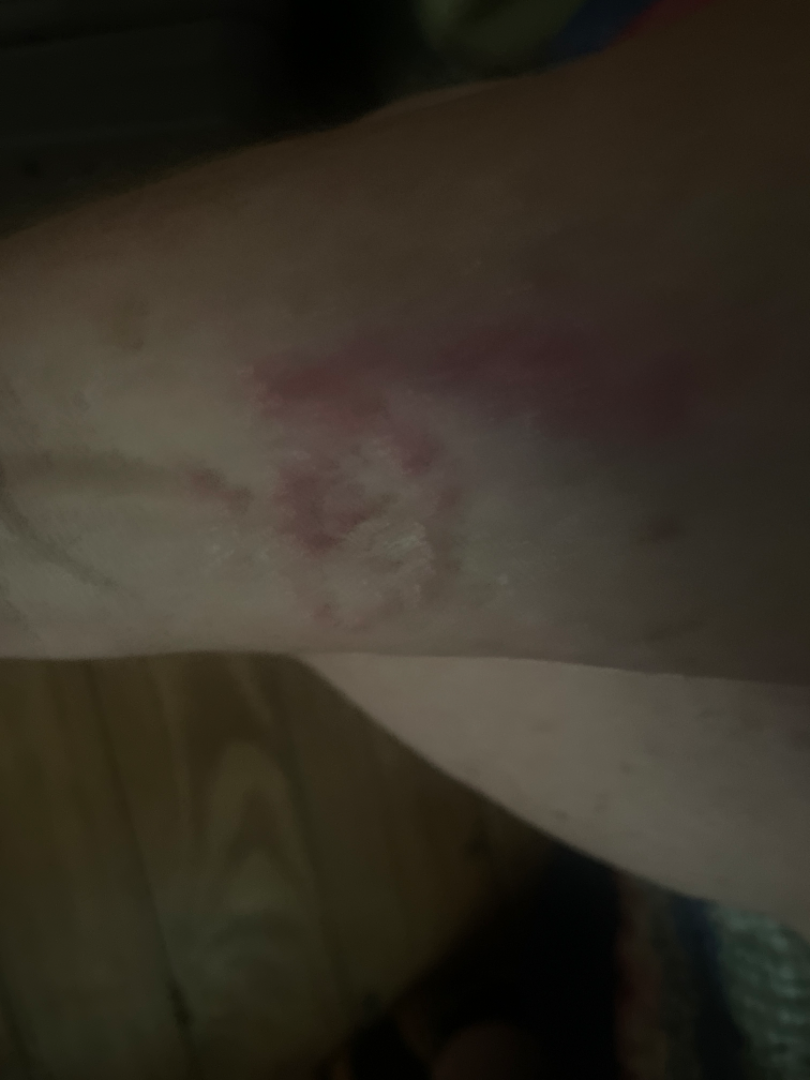No differential diagnosis could be assigned on photographic review.
The patient is a female aged 50–59.
Located on the arm.
The photograph is a close-up of the affected area.